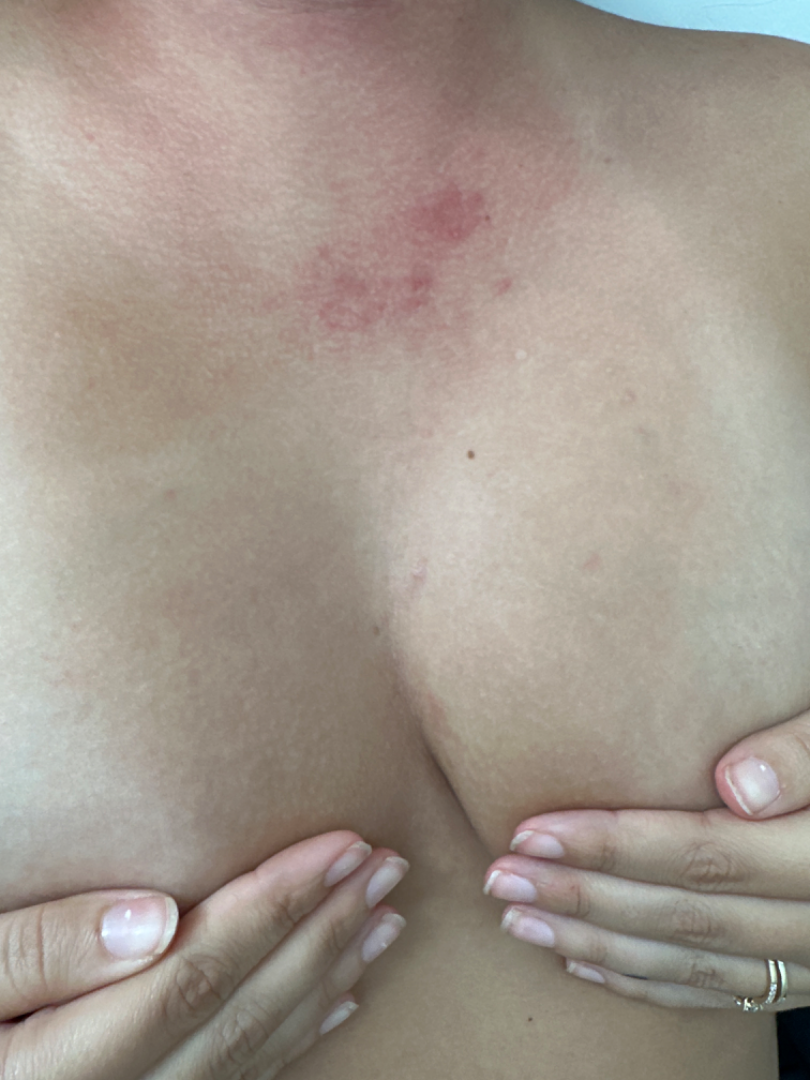assessment: indeterminate from the photograph.